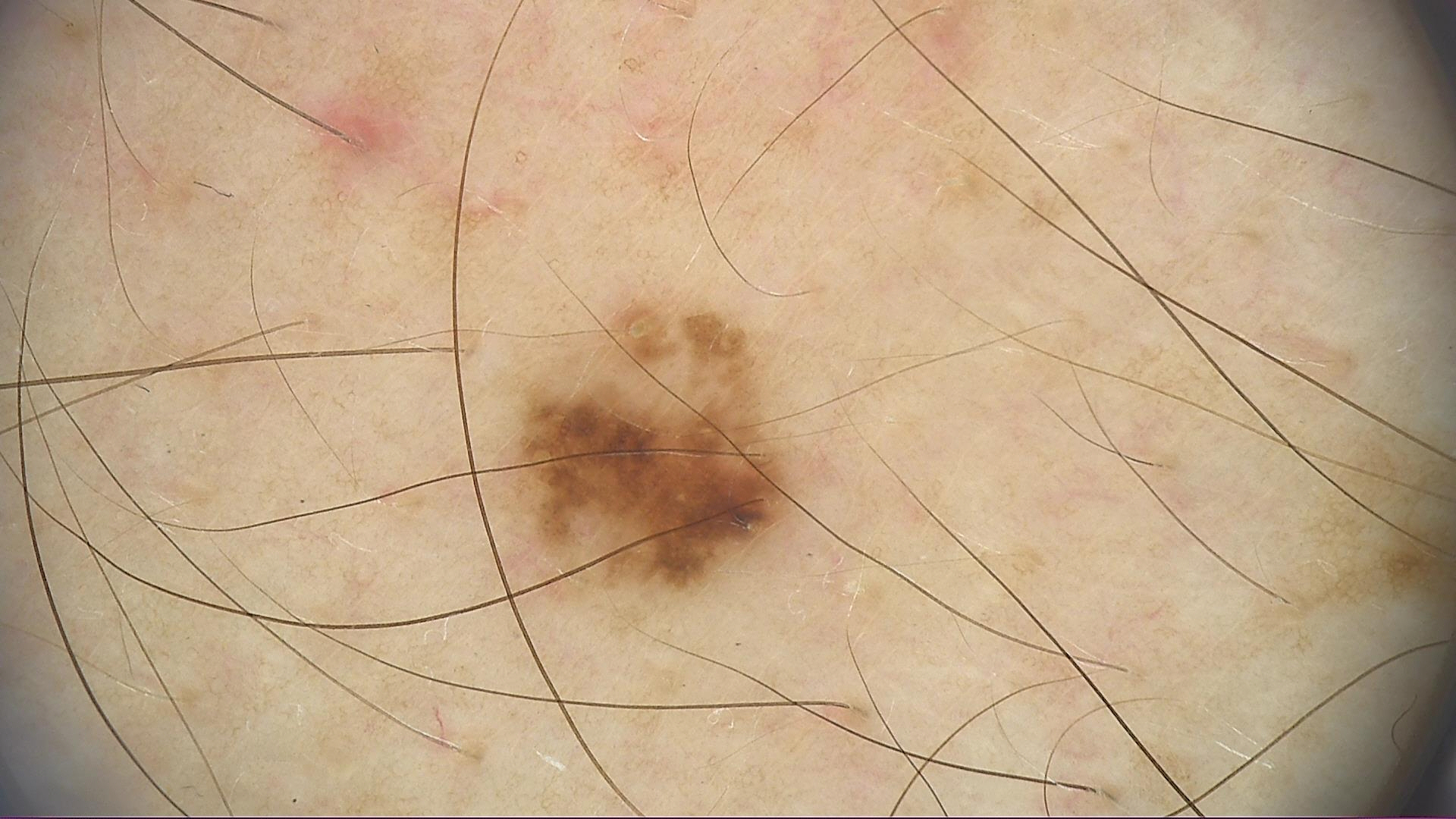The diagnostic label was a dysplastic junctional nevus.